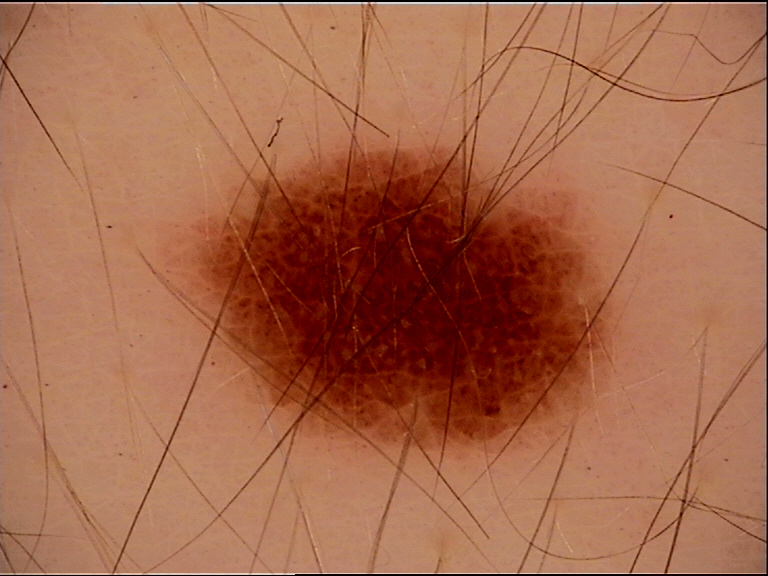A dermoscopic photograph of a skin lesion.
The diagnosis was a benign lesion — a dysplastic junctional nevus.